Female contributor, age 50–59 · this image was taken at an angle · the lesion involves the arm, back of the torso, leg and back of the hand.
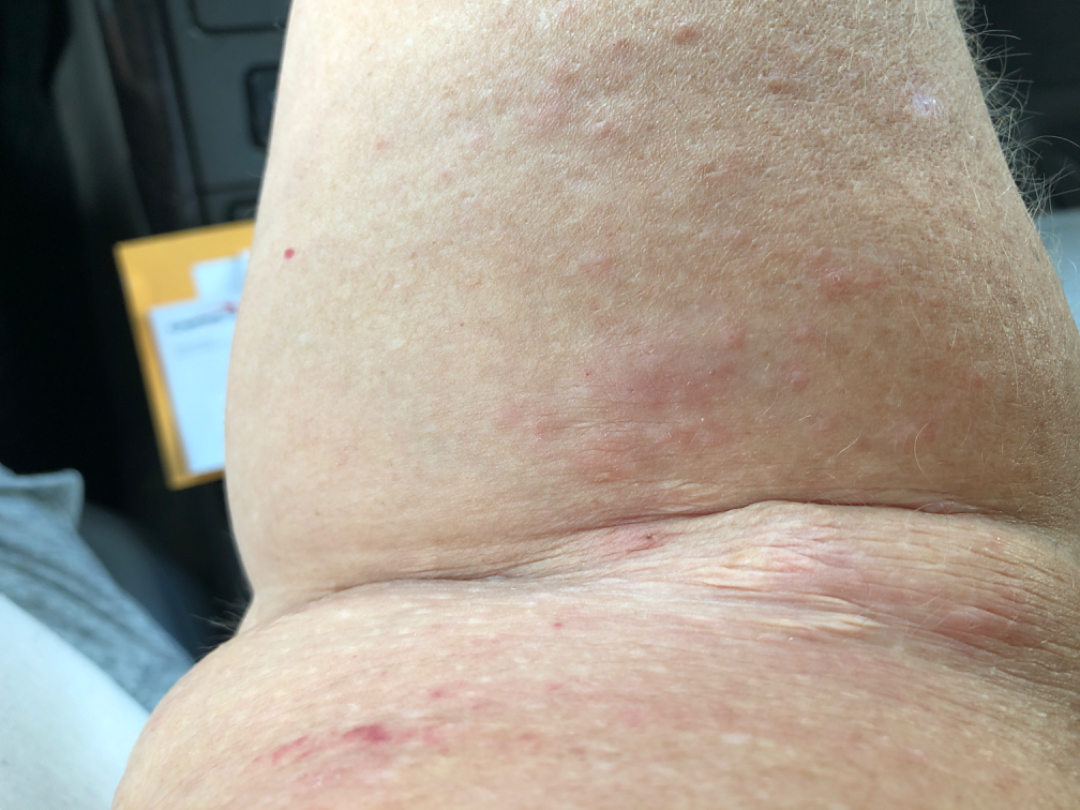Impression:
The reviewer was unable to grade this case for skin condition.
History:
The contributor notes enlargement, burning and itching. The patient also reports joint pain and fatigue. The contributor notes the condition has been present for three to twelve months. The patient considered this a rash. The lesion is described as raised or bumpy.